A female subject, aged 43 to 47. This is a dermoscopic photograph of a skin lesion.
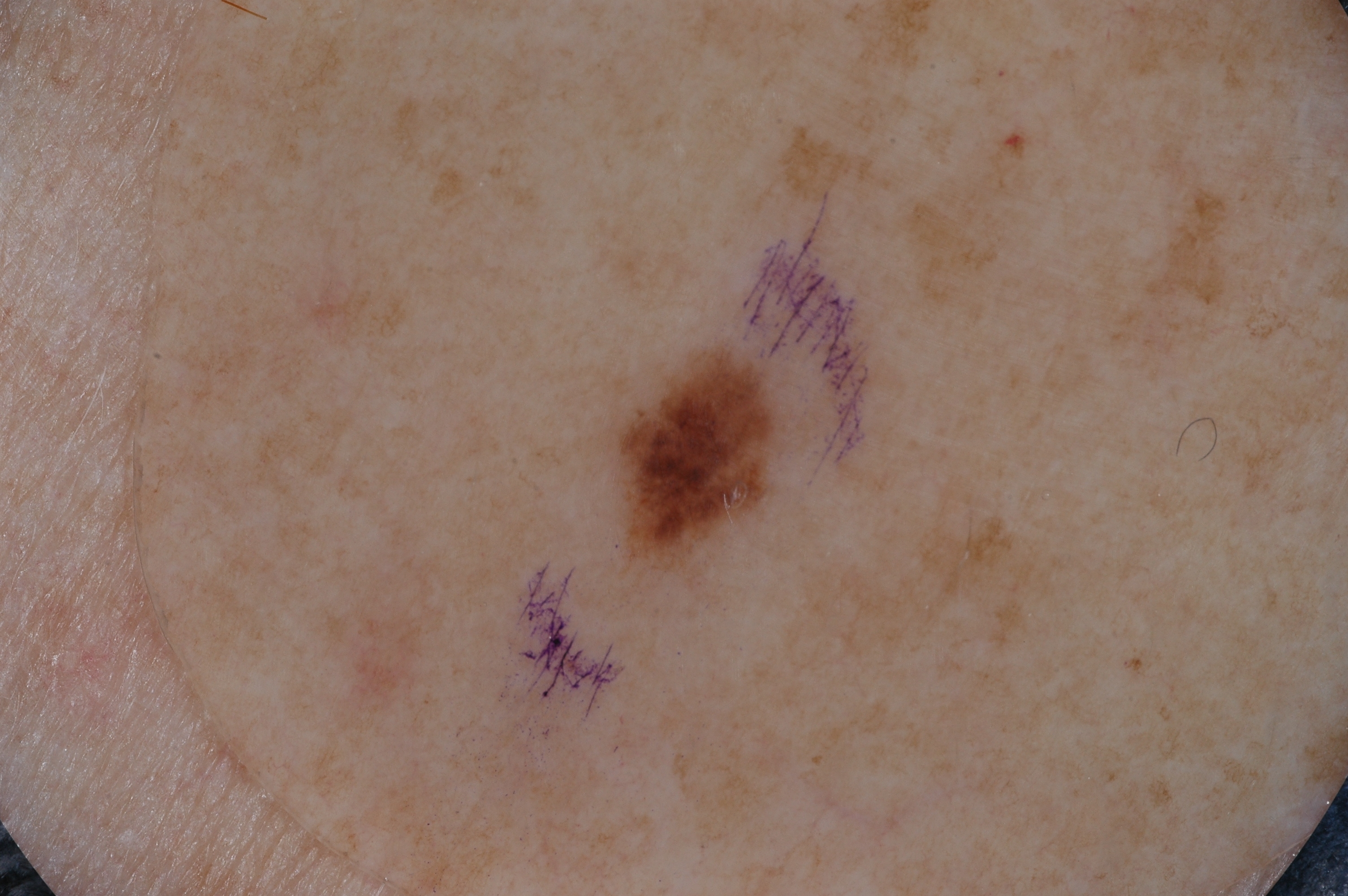location: left=622, top=357, right=769, bottom=546 | dermoscopic features not present: streaks, pigment network, milia-like cysts, and negative network | assessment: a melanocytic nevus, a benign lesion.